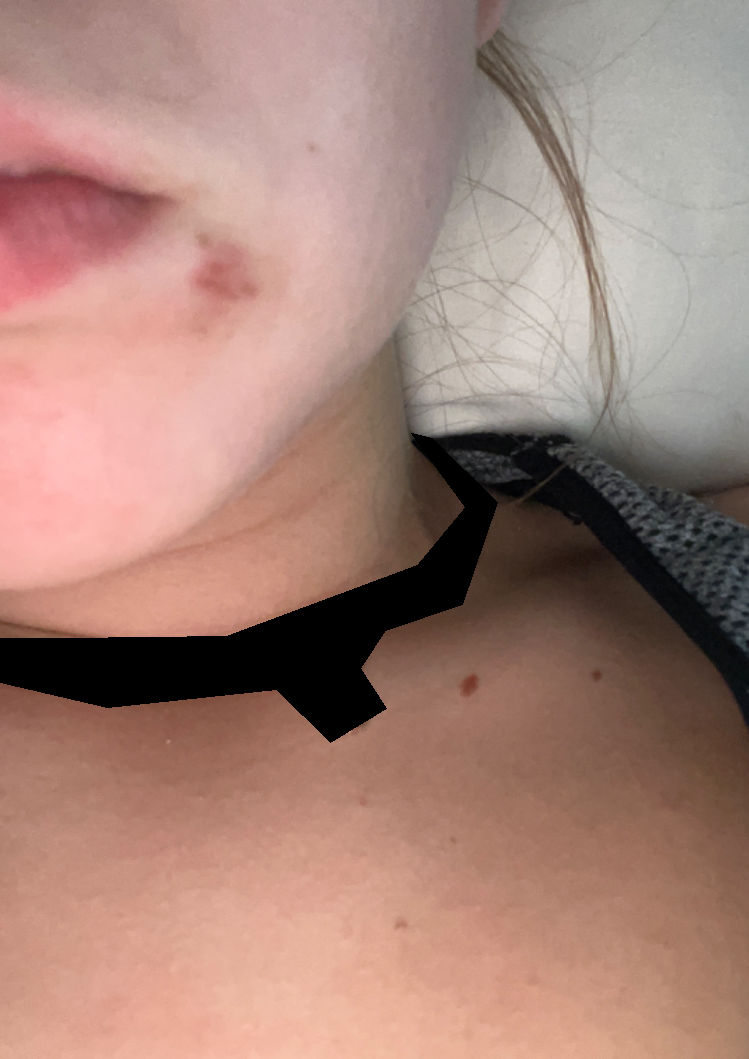Review: The skin findings could not be characterized from the image. Patient information: A close-up photograph.